A dermatoscopic image of a skin lesion.
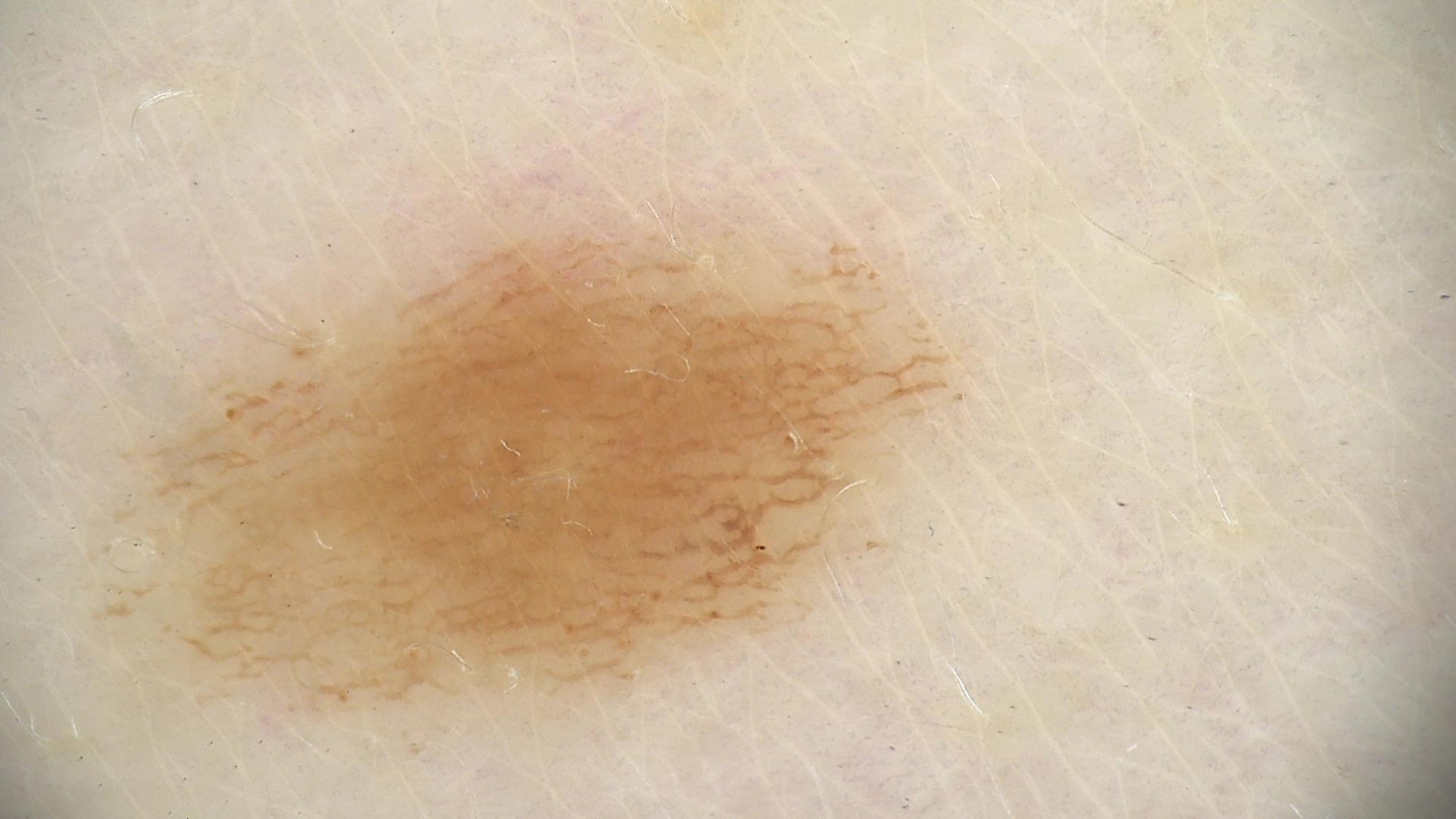The diagnostic label was a dysplastic junctional nevus.